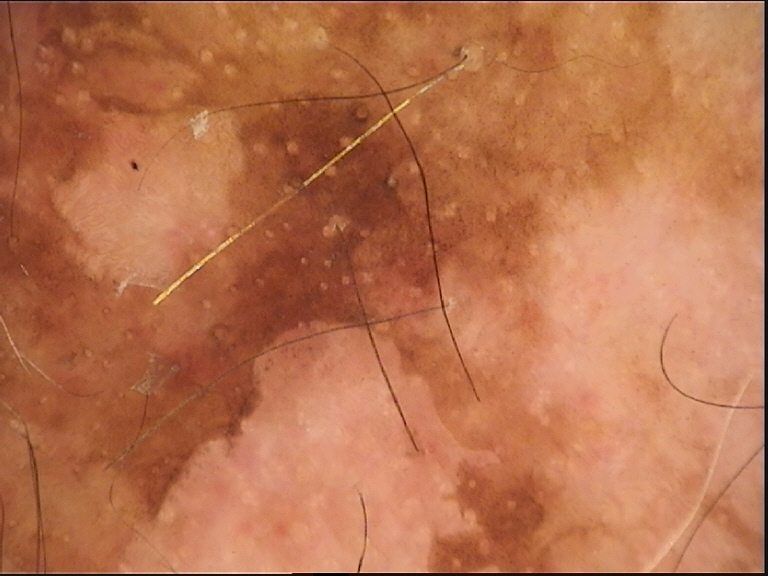Dermoscopy of a skin lesion.
The diagnosis was a seborrheic keratosis.